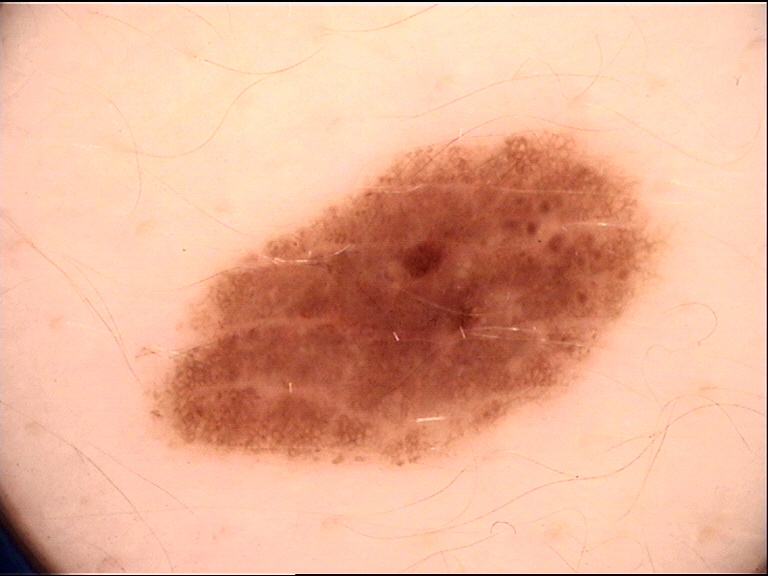Diagnosed as a dysplastic junctional nevus.